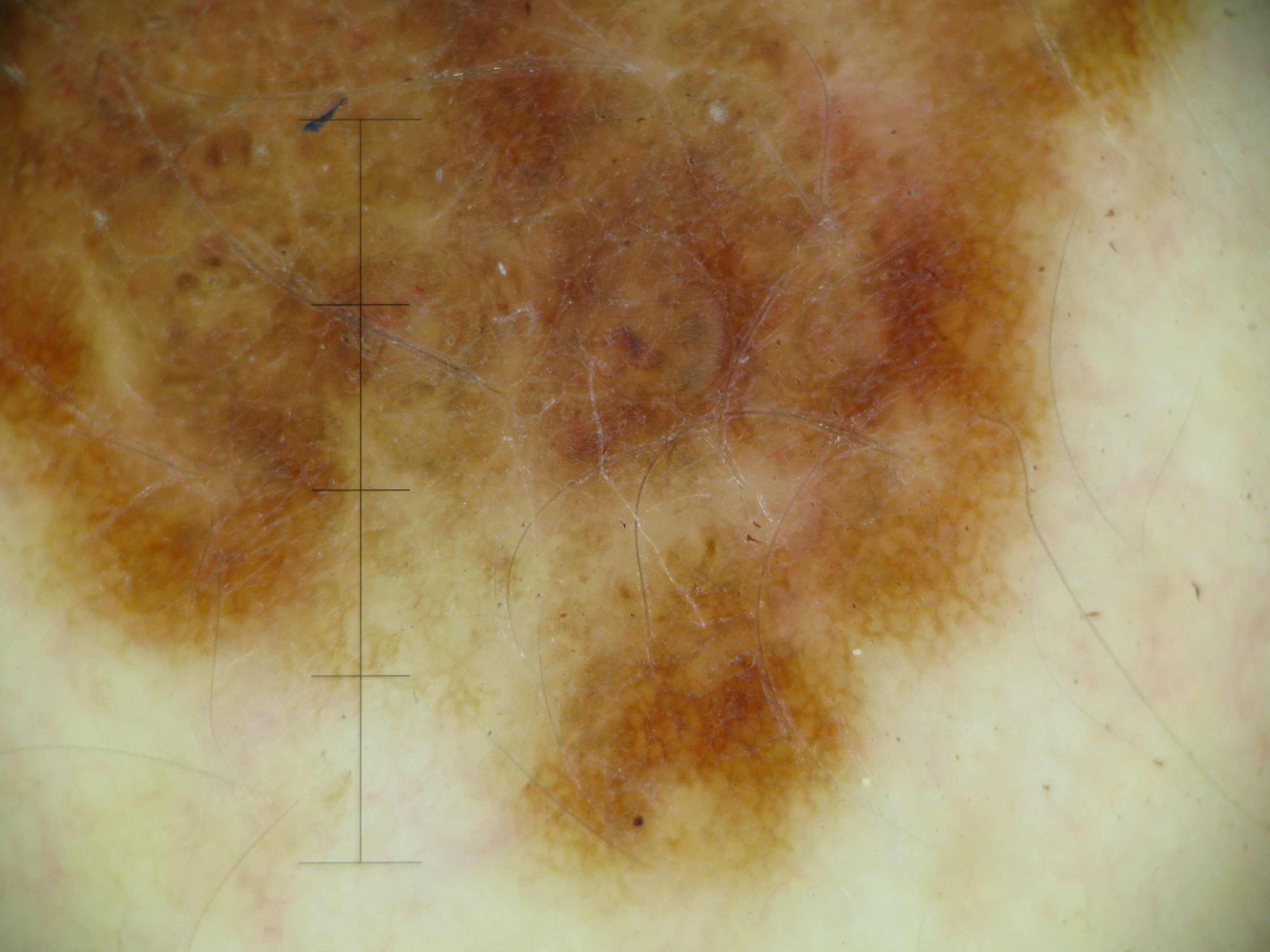image: dermoscopy, diagnostic label: melanoma (biopsy-proven).